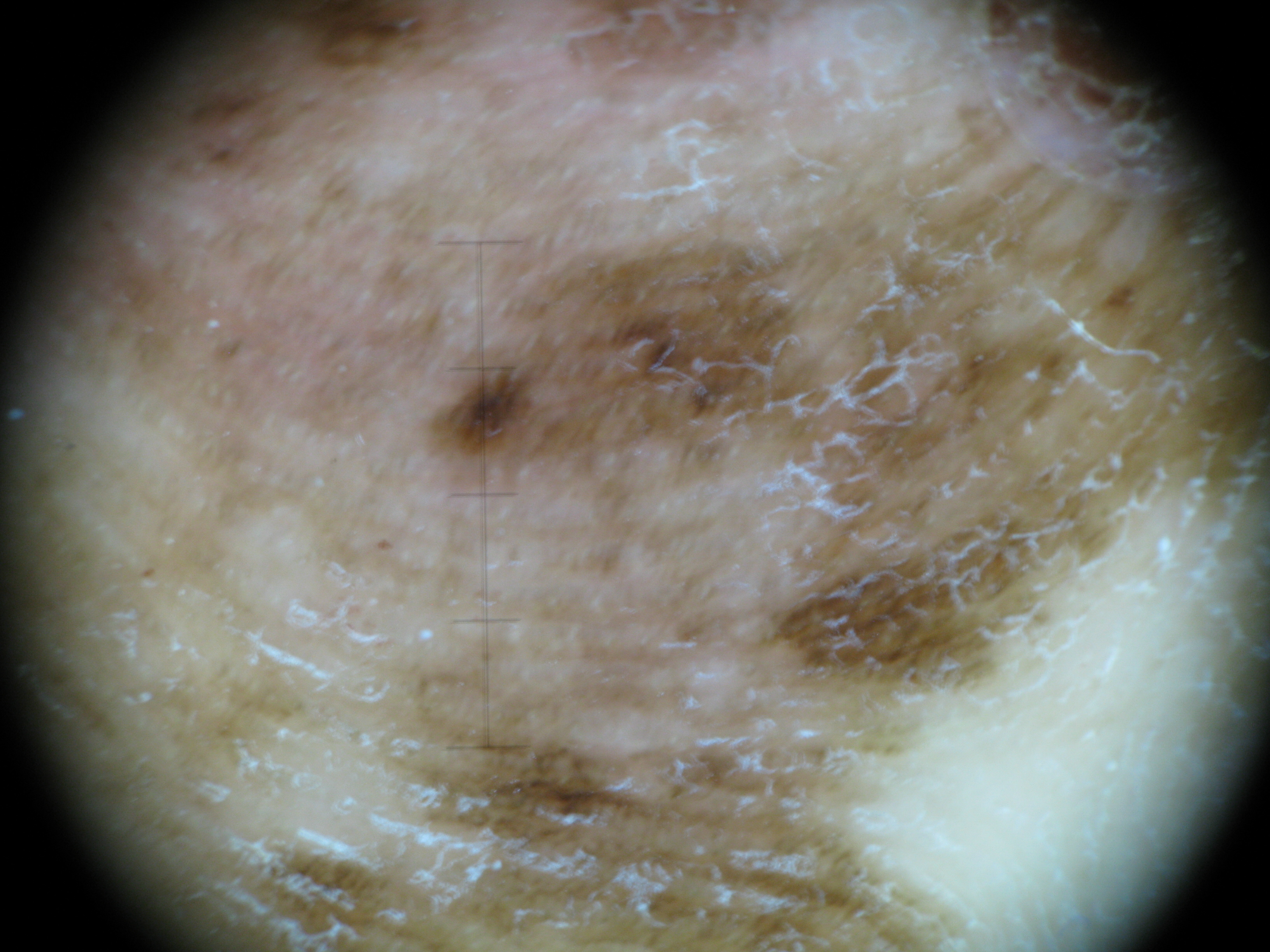Confirmed on histopathology as an acral lentiginous melanoma.